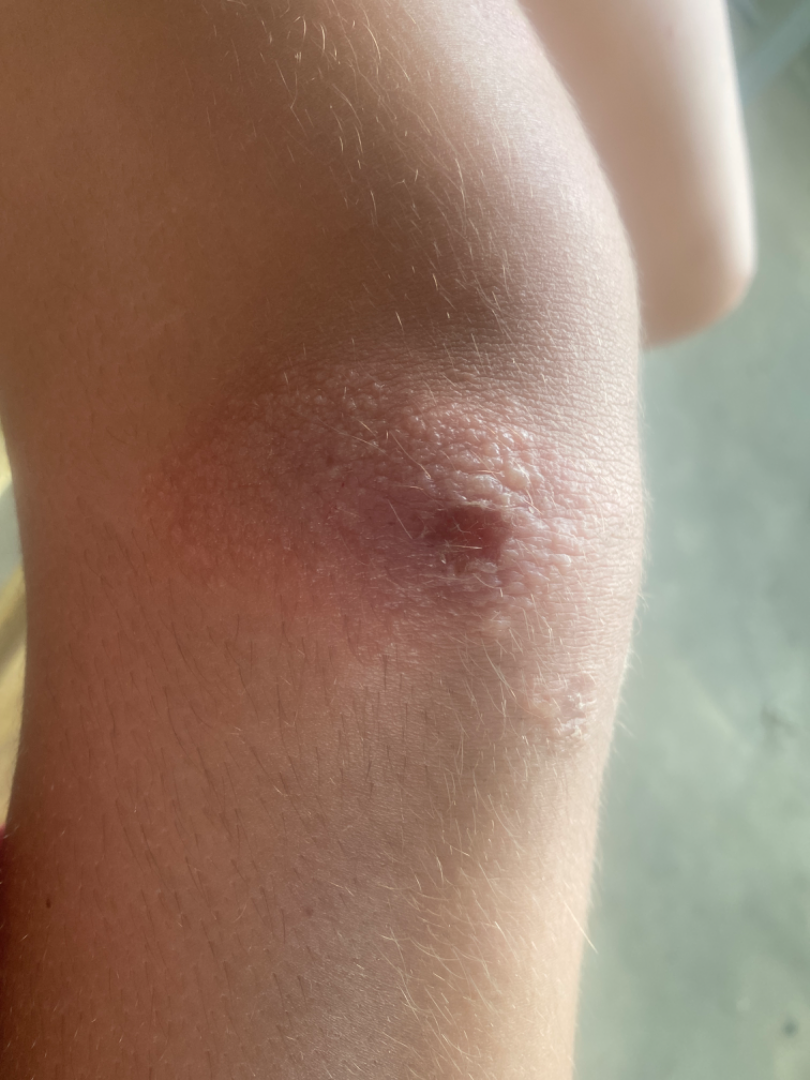Impression:
The image was not sufficient for the reviewer to characterize the skin condition.